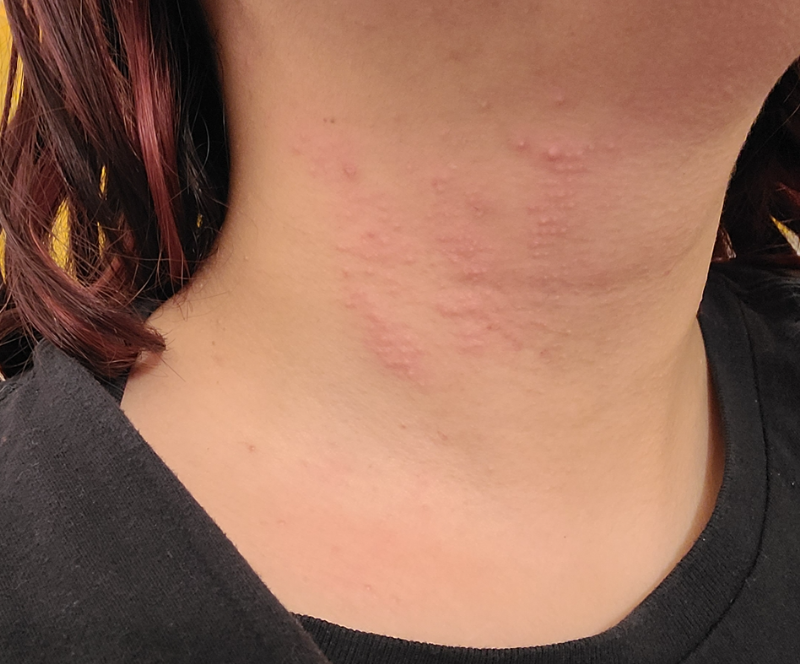assessment=a single dermatologist reviewed the case: the differential includes Allergic Contact Dermatitis and Irritant Contact Dermatitis, with no clear leading consideration.